A close-up photograph · the patient is 30–39, female · the affected area is the arm: 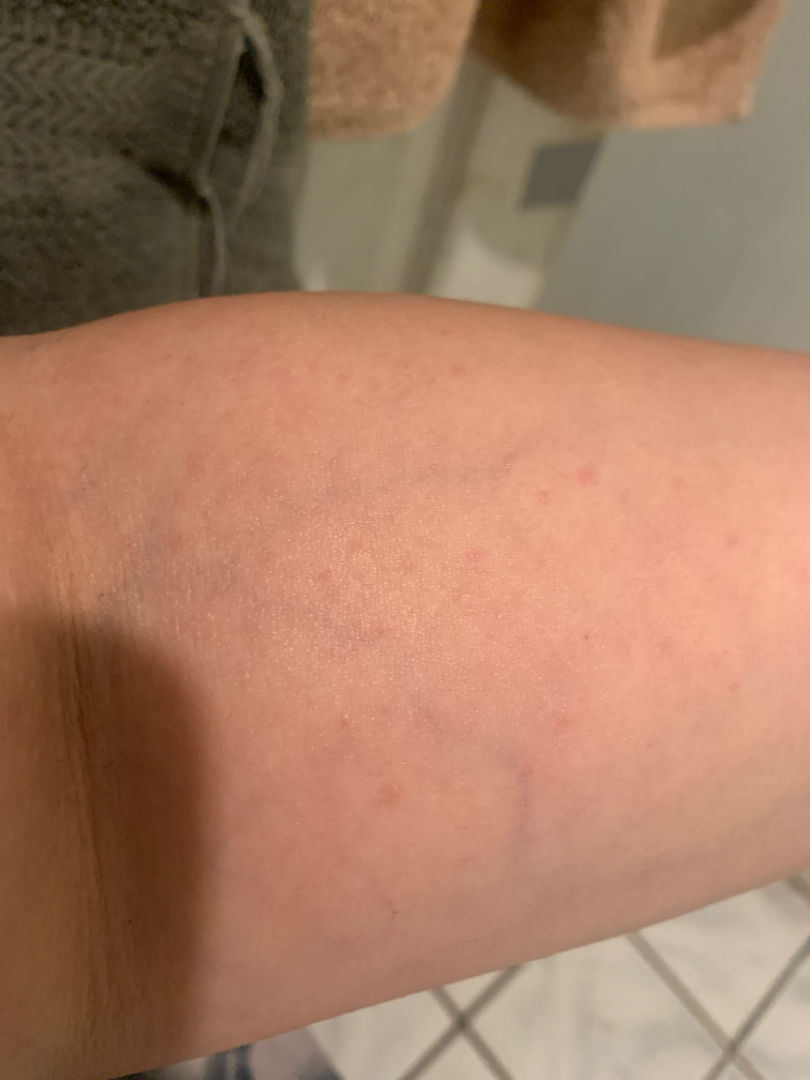Clinical context: The patient described the issue as a rash. No constitutional symptoms were reported. The lesion is described as raised or bumpy. Present for about one day. Symptoms reported: bothersome appearance. Assessment: The leading consideration is Insect Bite; possibly Eczema; an alternative is Molluscum Contagiosum.